A dermoscopic close-up of a skin lesion. A female patient aged 58 to 62:
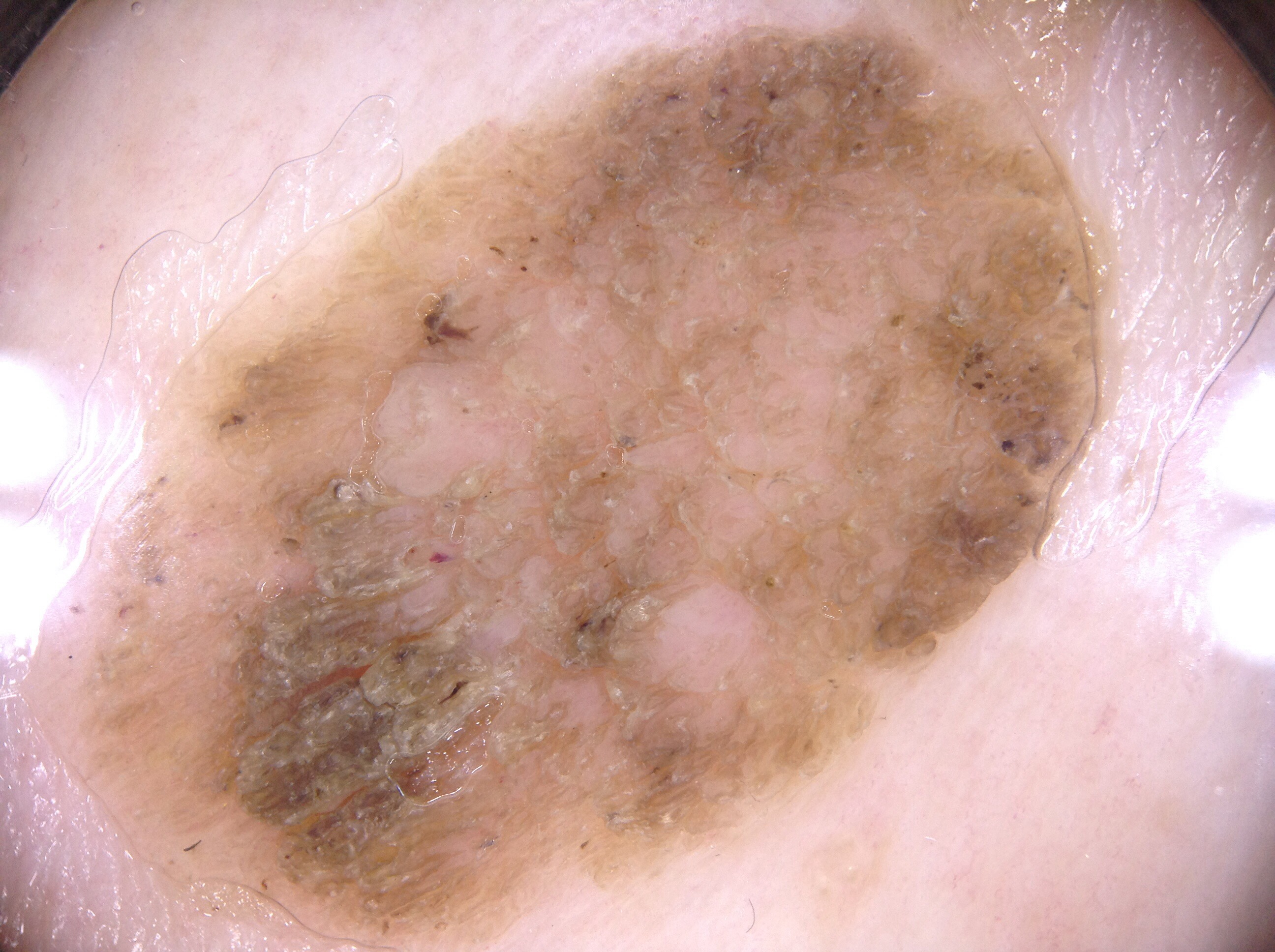size: large
lesion location: left=20, top=2, right=1125, bottom=950
absent dermoscopic findings: streaks, milia-like cysts, pigment network, and negative network
diagnostic label: a seborrheic keratosis, a benign skin lesion